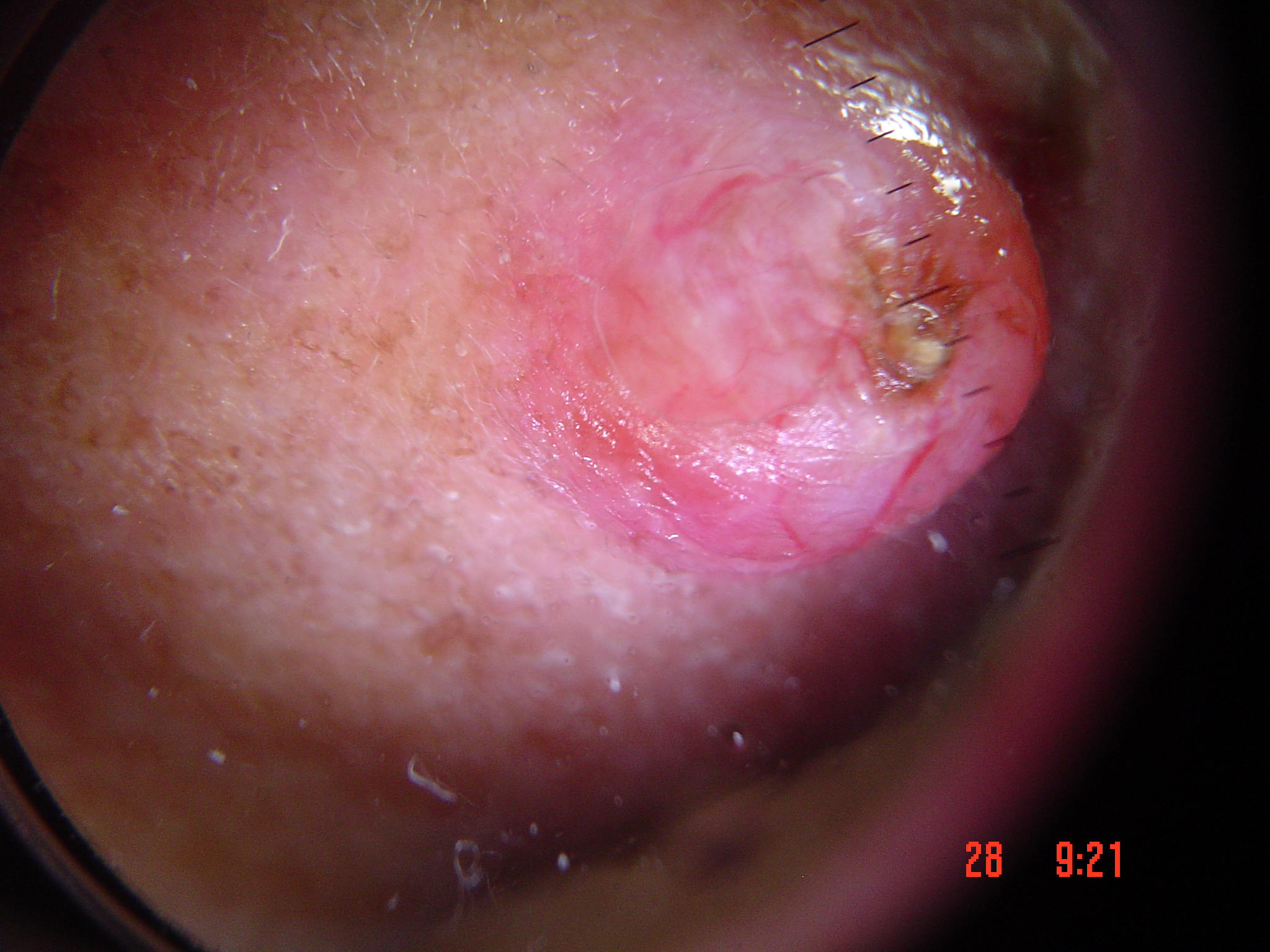A dermoscopic image of a skin lesion.
Confirmed on histopathology as a basal cell carcinoma.